The contributor reports itching · this image was taken at a distance · the affected area is the arm.
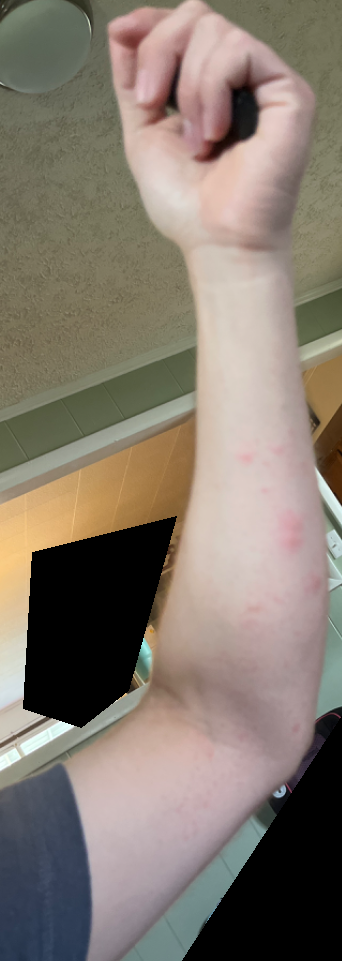On teledermatology review: most likely Urticaria; possibly Insect Bite.